The arm and back of the hand are involved. The photo was captured at an angle. The contributor is 60–69, female.
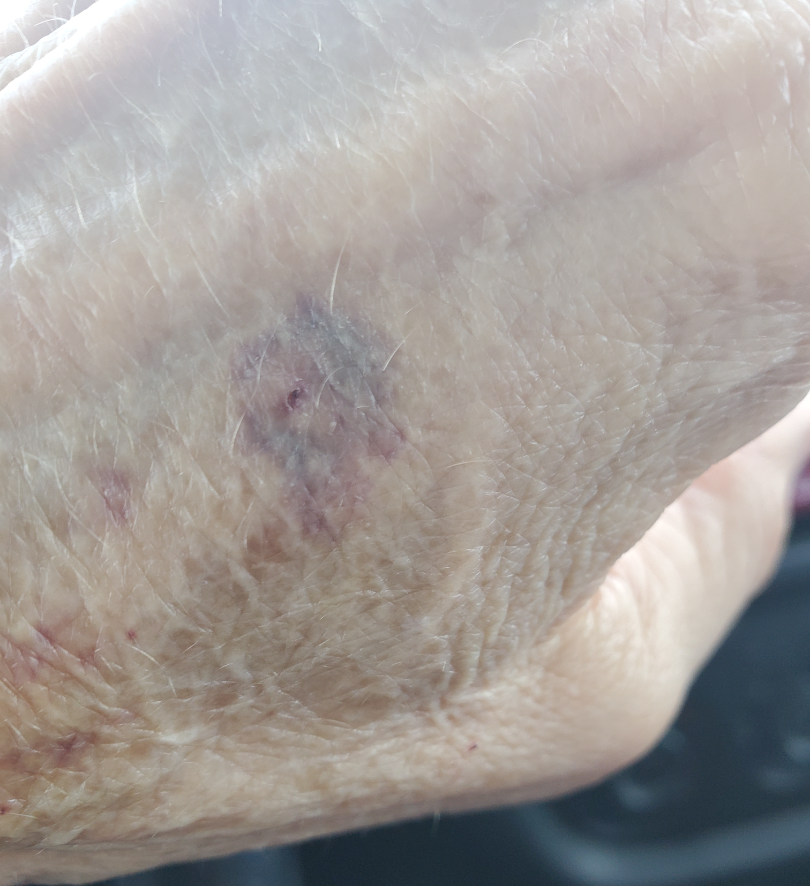The lesion is associated with bothersome appearance and bleeding. The patient considered this a rash. No constitutional symptoms were reported. Present for more than five years. The patient indicates the lesion is fluid-filled. One reviewing dermatologist: in keeping with ecchymoses.